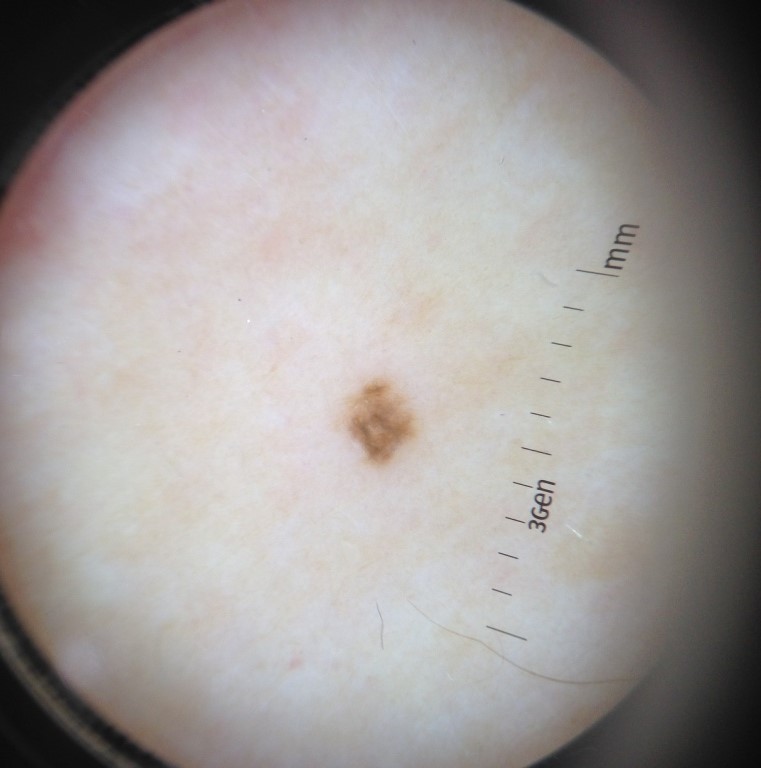Conclusion: Classified as a dysplastic junctional nevus.